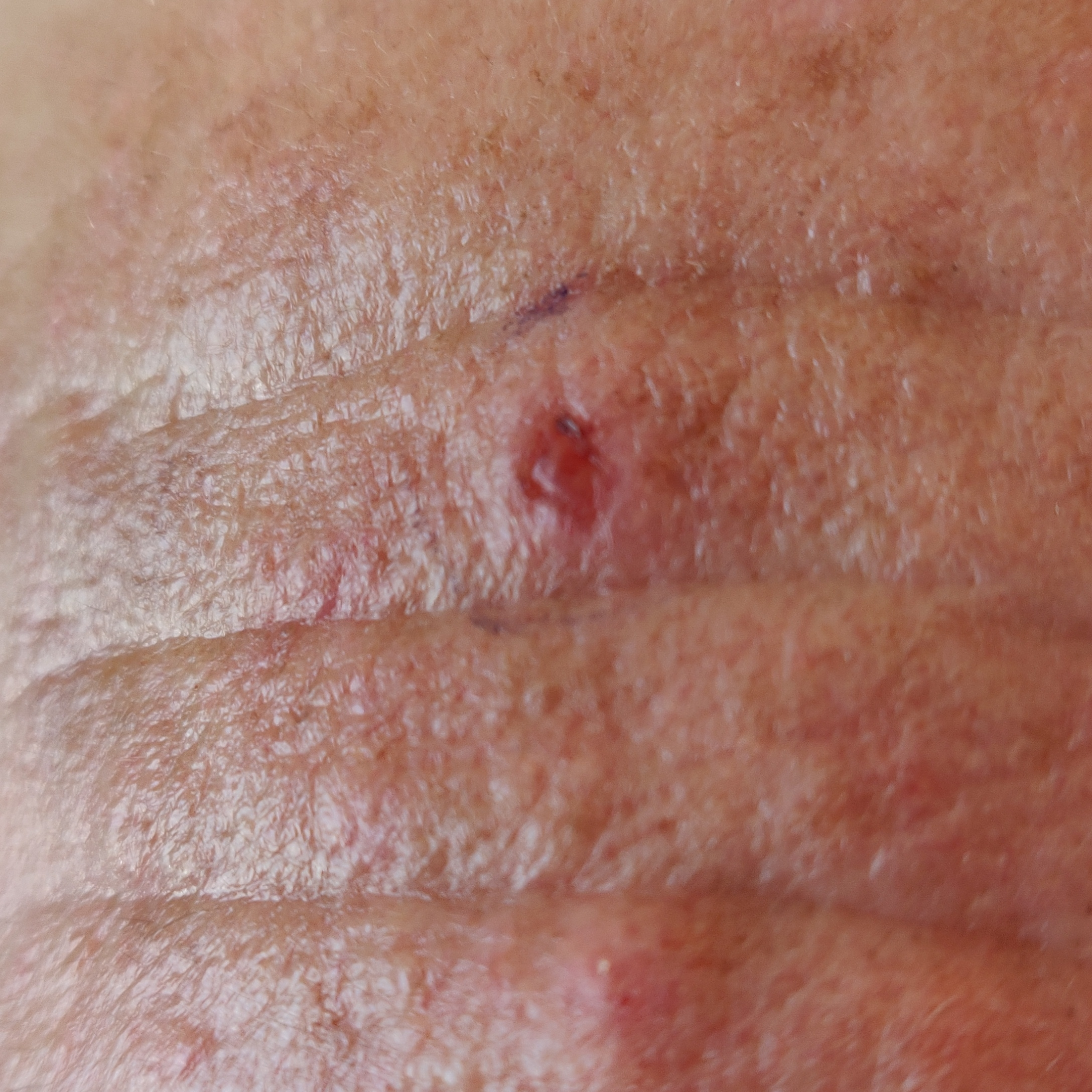FST: II; risk factors: prior malignancy (patient or family), pesticide exposure; patient: male, aged 58; body site: the face; size: approx. 6 × 5 mm; patient-reported symptoms: bleeding, growth, itching; pathology: basal cell carcinoma (biopsy-proven).